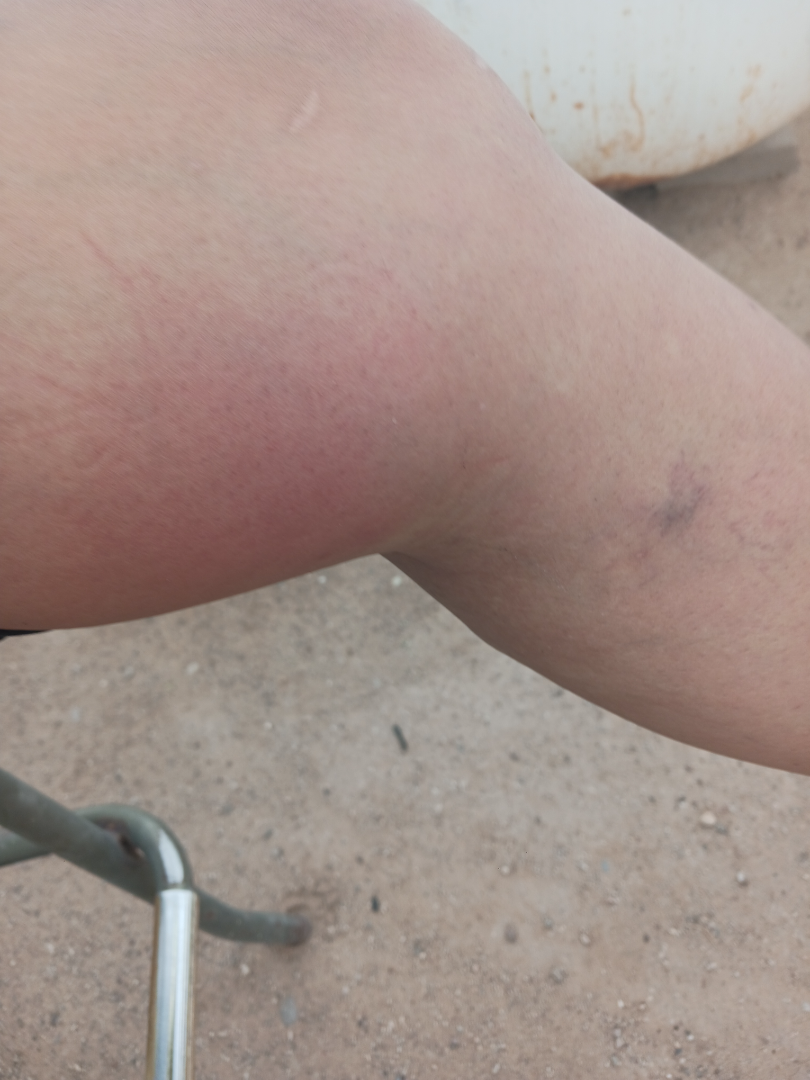{"patient_category": "acne", "body_site": "leg", "duration": "about one day", "shot_type": "close-up", "patient": "female", "texture": "fluid-filled", "differential": {"tied_lead": ["Cellulitis", "Eczema"], "unlikely": ["Insect Bite", "deep vein thrombosis"]}}